A dermoscopic image of a skin lesion.
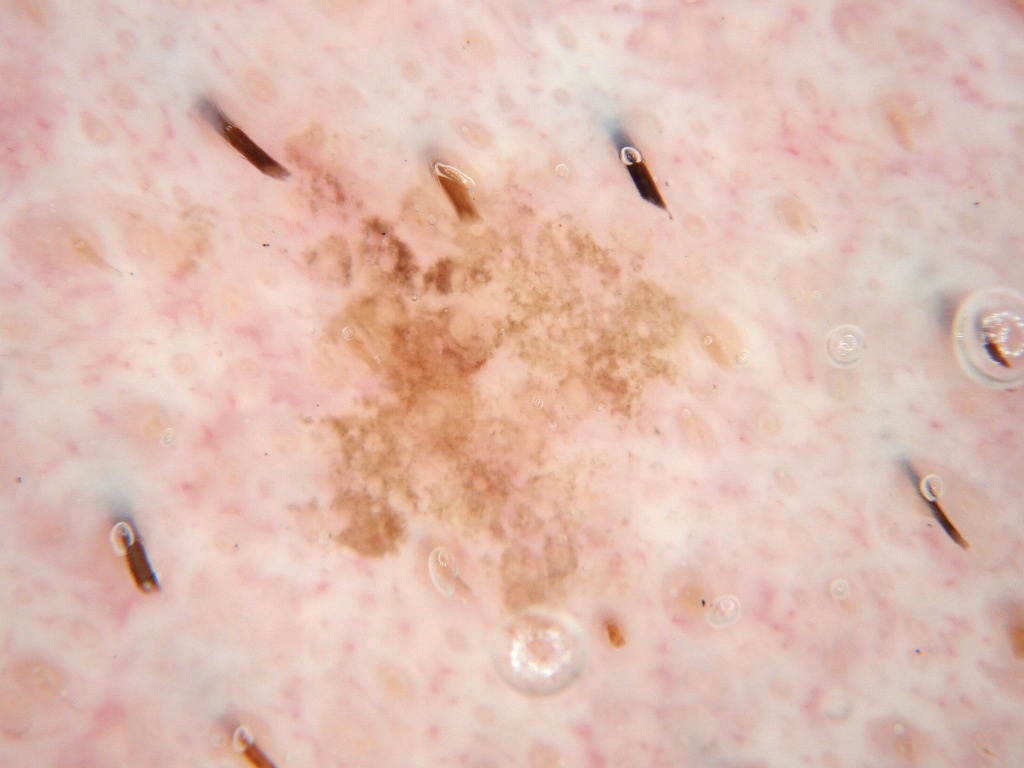lesion location: [239, 111, 763, 687] | absent dermoscopic findings: milia-like cysts, streaks, pigment network, negative network, and globules | diagnostic label: a melanocytic nevus, a benign lesion.